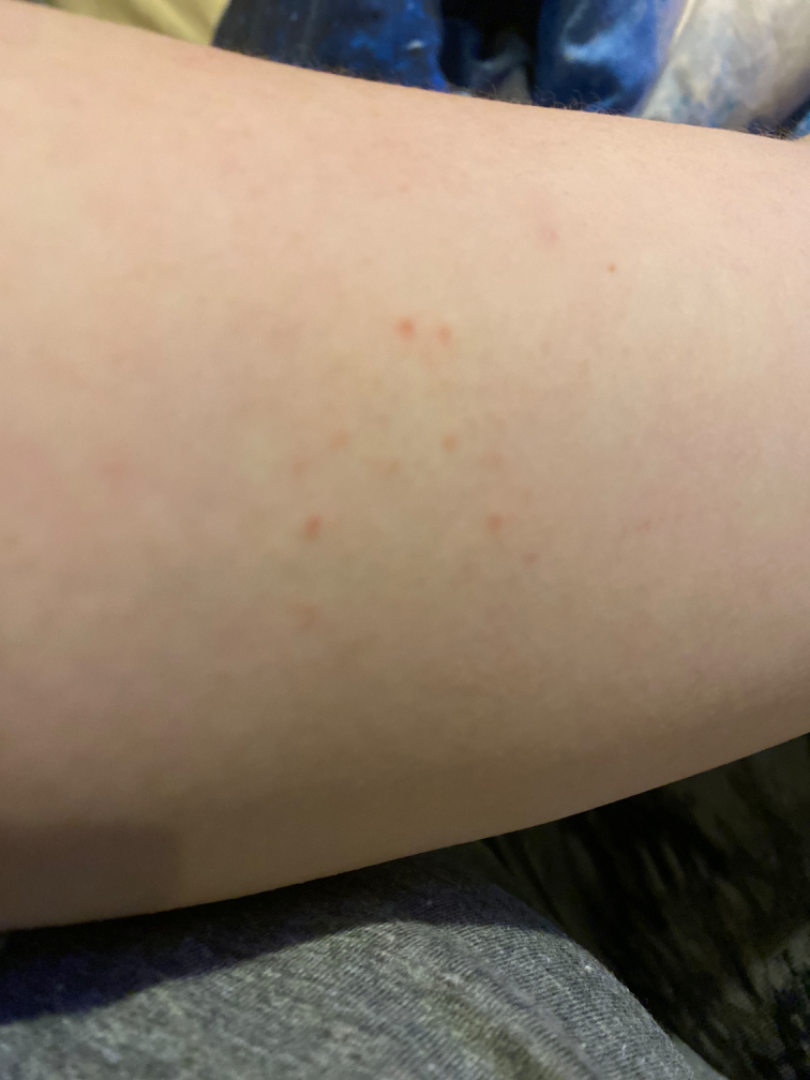No differential diagnosis could be assigned on photographic review.